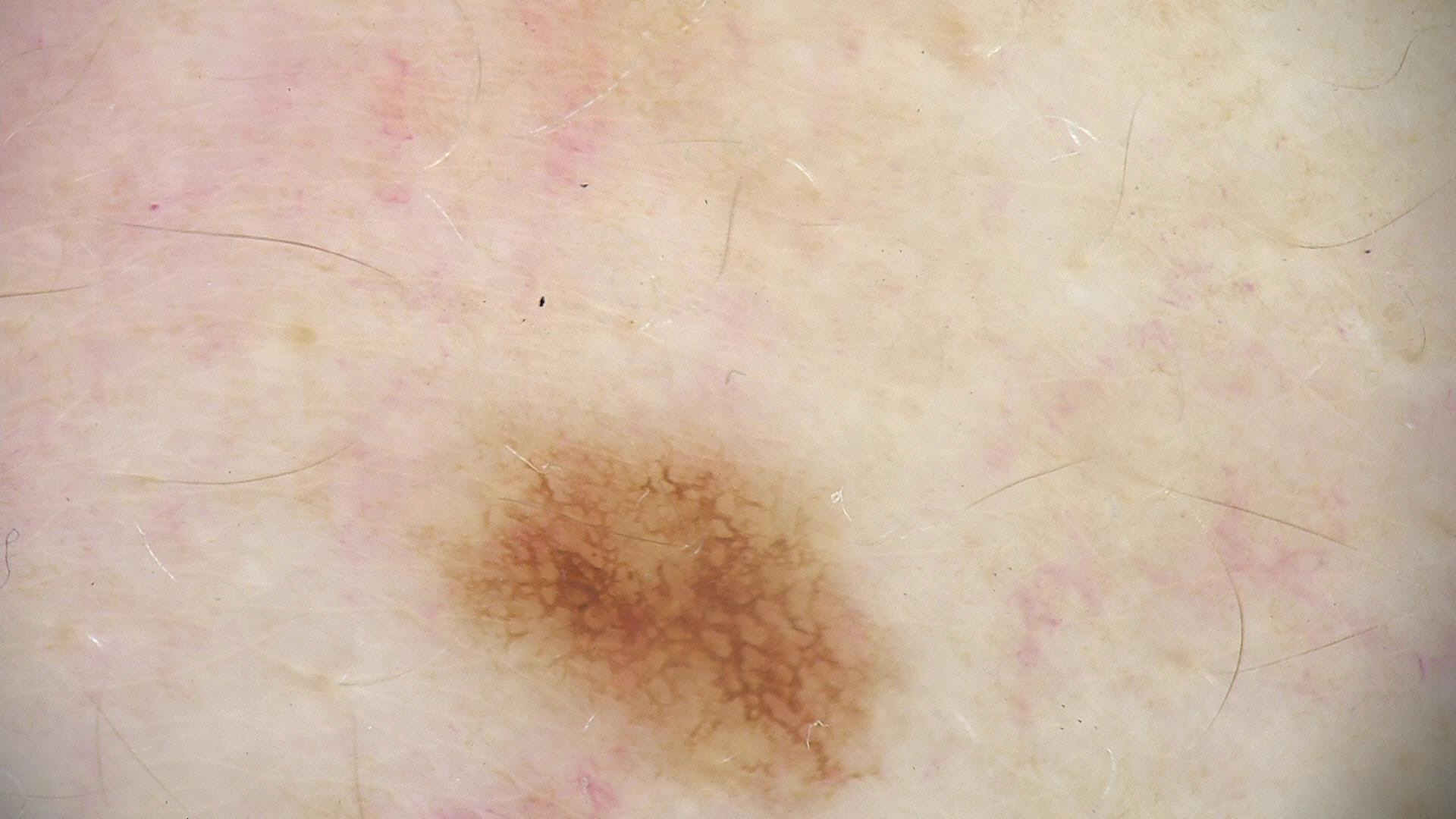image: dermatoscopy, diagnostic label: dysplastic junctional nevus (expert consensus).